A dermoscopic close-up of a skin lesion.
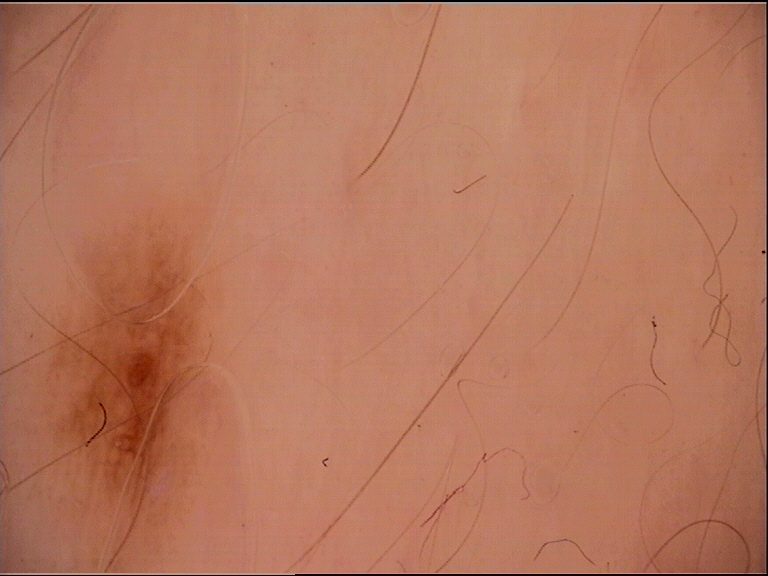This is a banal lesion. Classified as a junctional nevus.